A dermatoscopic image of a skin lesion: 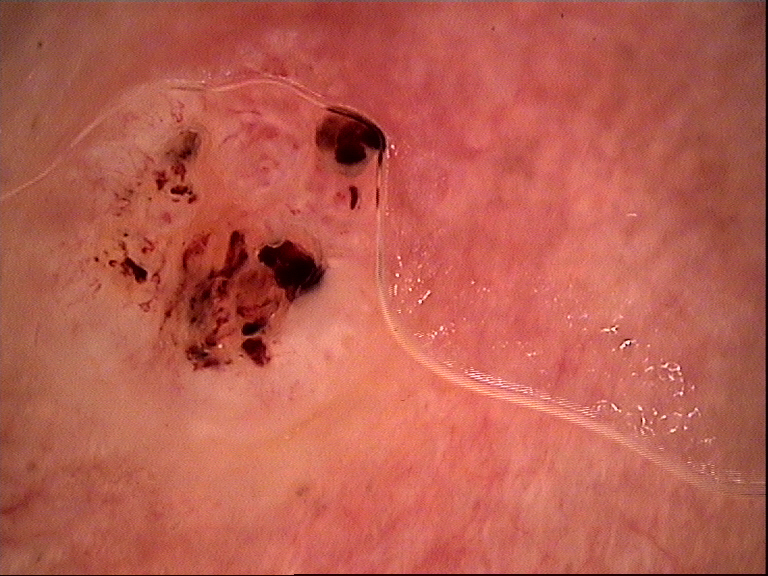diagnosis = basal cell carcinoma (biopsy-proven).